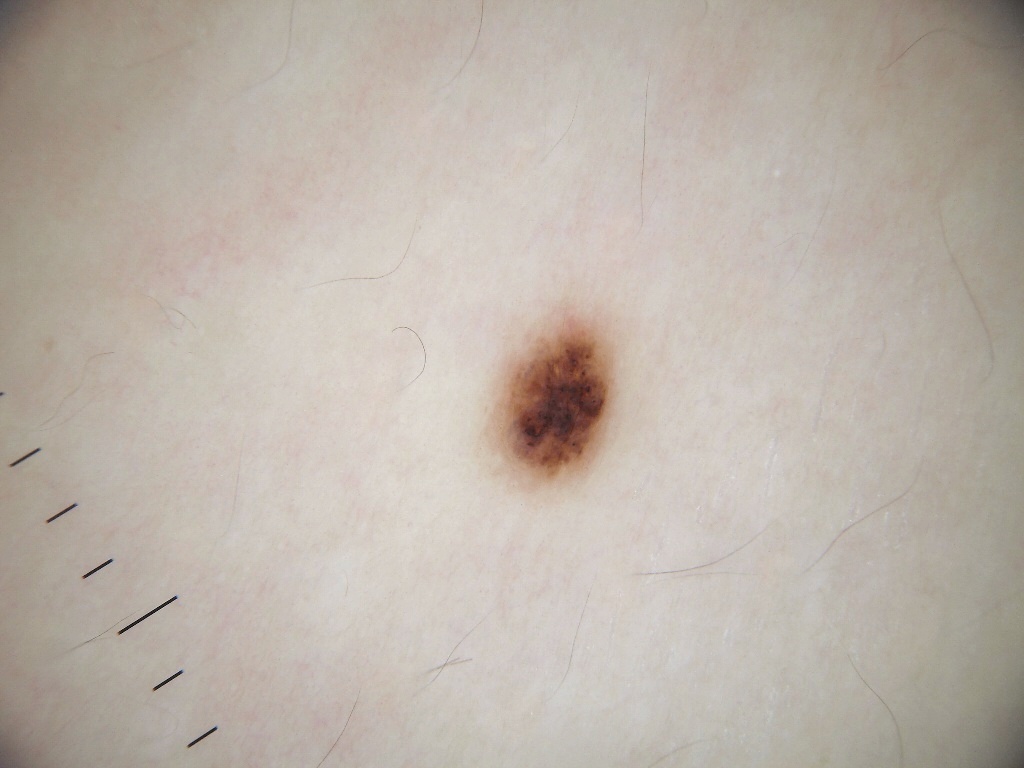Dermoscopy of a skin lesion. The subject is a female about 15 years old. The dermoscopic pattern shows no negative network, globules, milia-like cysts, pigment network, or streaks. As (left, top, right, bottom), the lesion is bounded by [491,307,617,487]. Diagnosed as a melanocytic nevus, a benign lesion.